A male patient approximately 75 years of age · FST II — 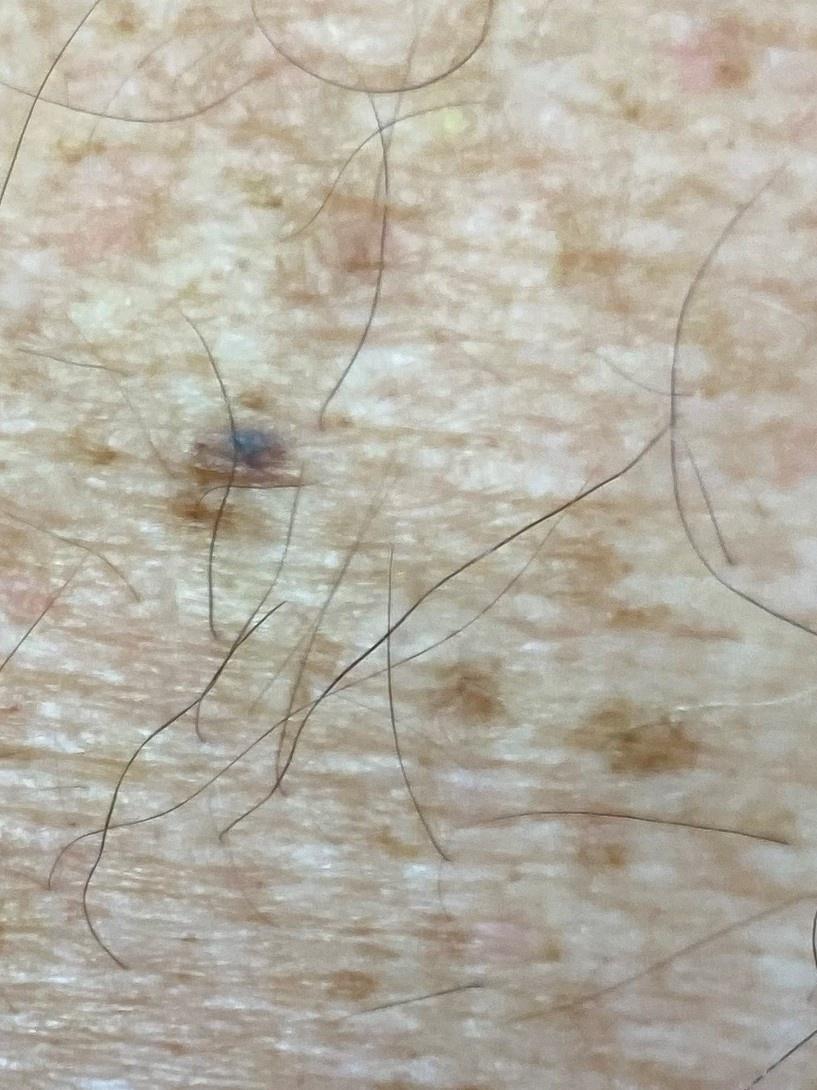Located on the trunk. On biopsy, the diagnosis was a benign lesion — a nevus.